The patient reported no systemic symptoms, the patient is a female aged 50–59, located on the arm, the lesion is described as raised or bumpy, the photo was captured at an angle: 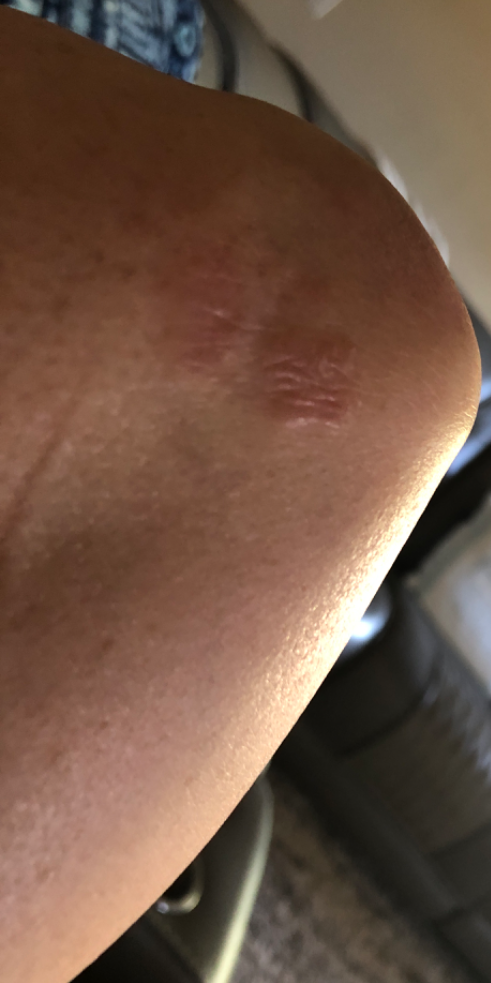The dermatologist could not determine a likely condition from the photograph alone.